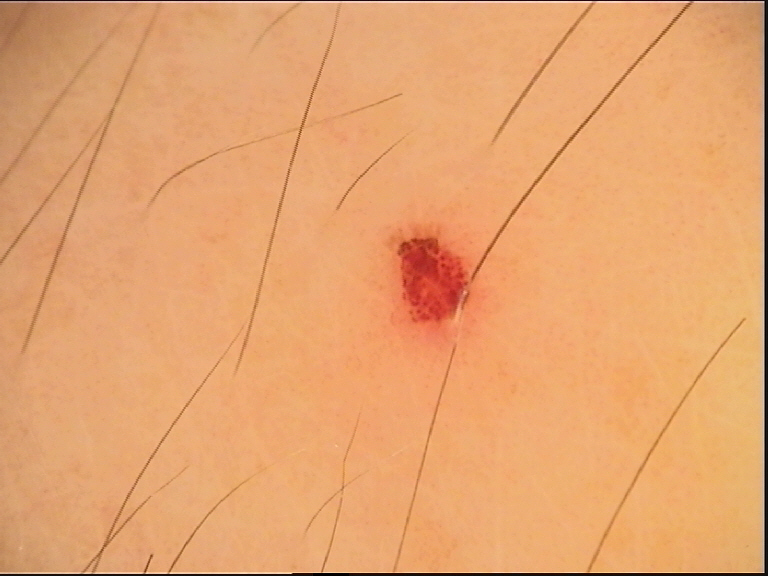assessment — hemangioma (expert consensus)